The photo was captured at an angle: 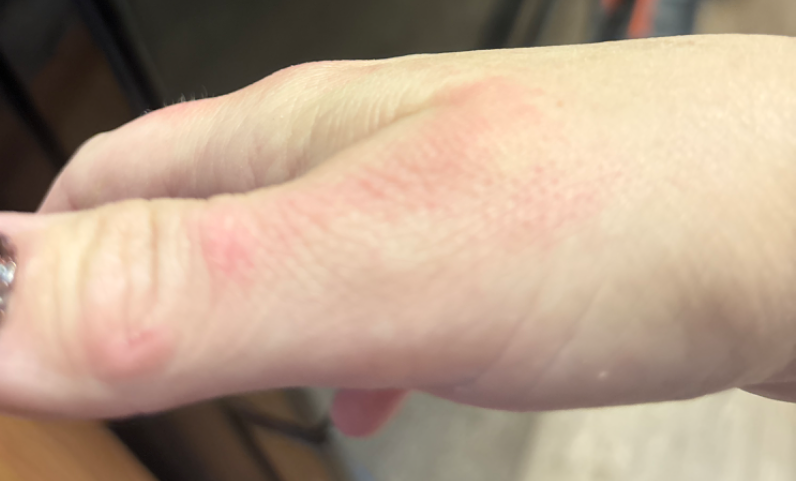Q: What is the dermatologist's impression?
A: a single dermatologist reviewed the case: the reviewer's impression was Eczema